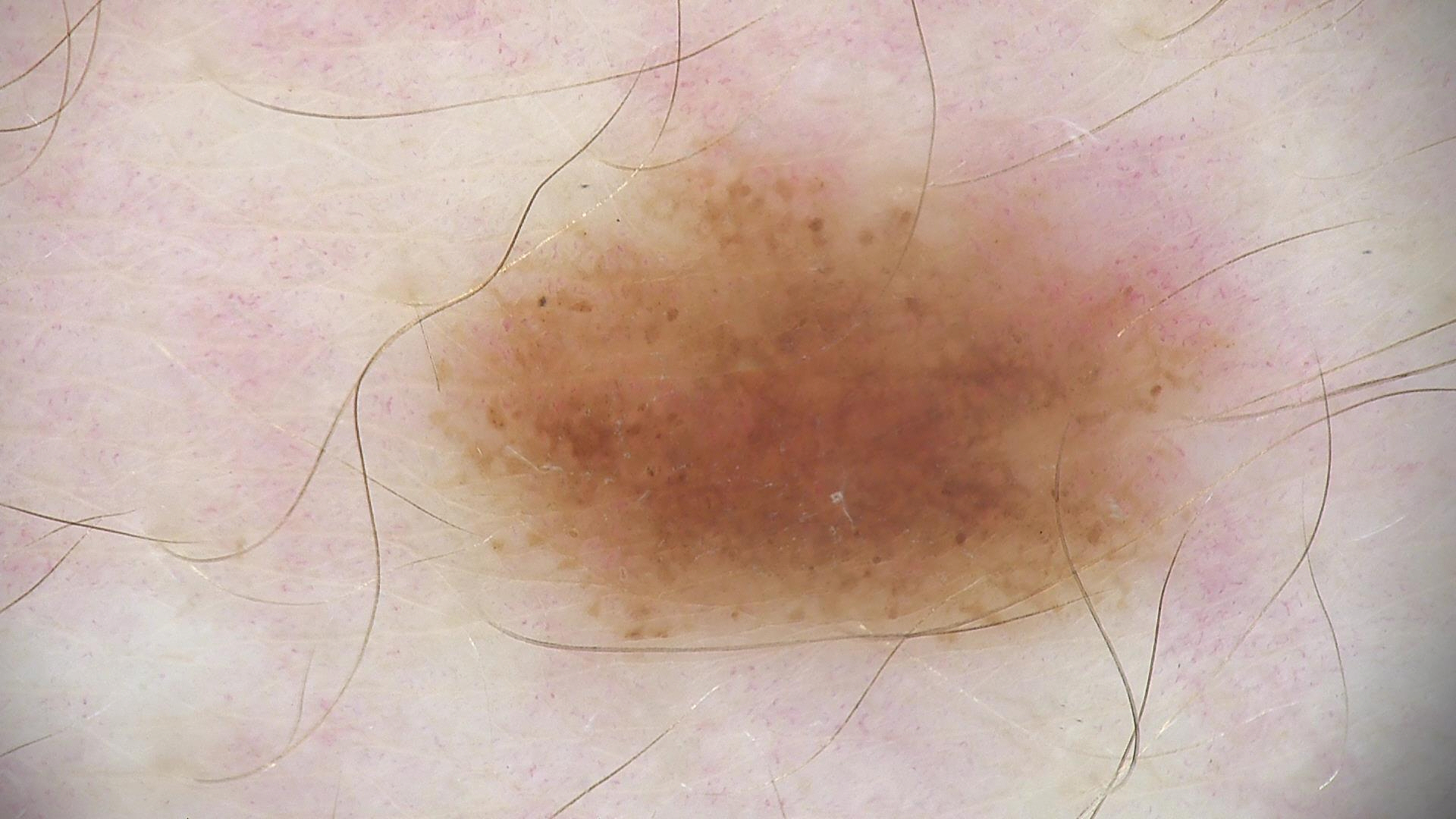Diagnosis: Confirmed on histopathology as a melanoma.